A dermoscopic image of a skin lesion: 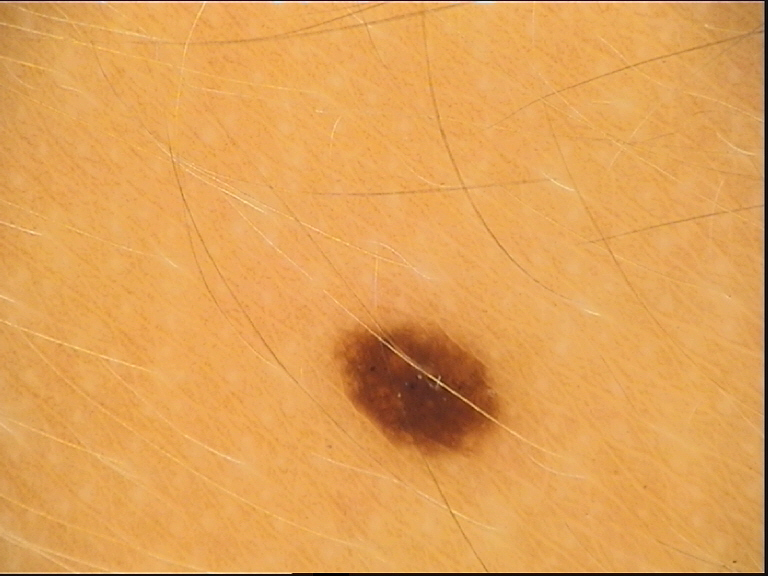class = dysplastic junctional nevus (expert consensus).